This is a close-up image · the subject is a female aged 40–49 — 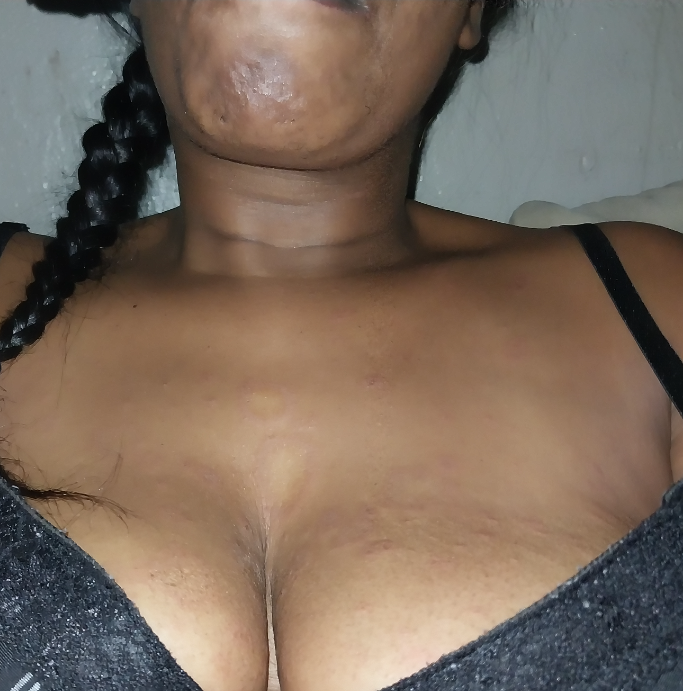On remote review of the image: Scar Condition (considered); Pityriasis rosea (considered); Psoriasis (unlikely); Eczema (unlikely).